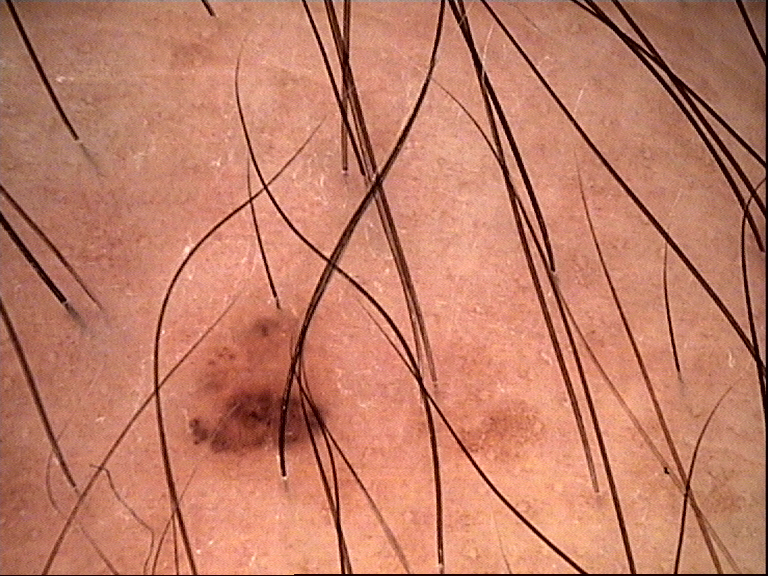label = compound nevus (expert consensus).